The patient is a female aged 18–29 · this image was taken at a distance · located on the leg.
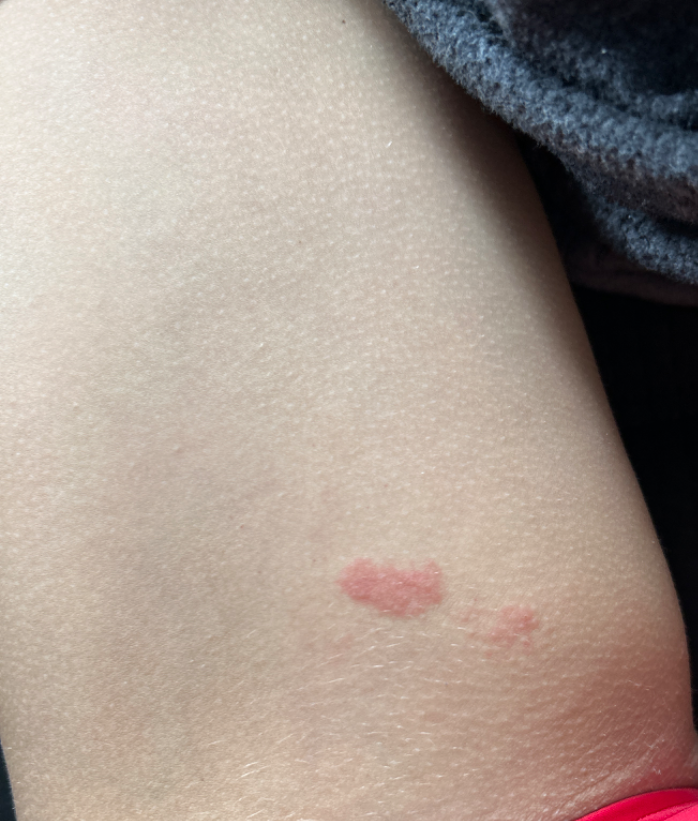Assessment:
The reviewing dermatologist was unable to assign a differential diagnosis from the image.